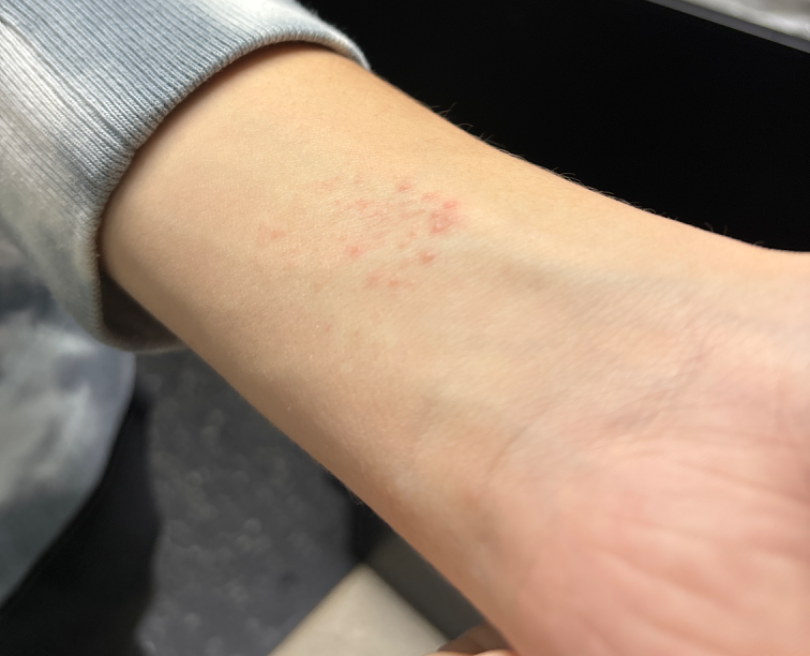History:
An image taken at an angle. The patient considered this acne. The affected area is the arm. Reported duration is about one day. The patient reports the lesion is fluid-filled and raised or bumpy. Skin tone: human graders estimated 3 on the Monk skin tone scale. No associated lesion symptoms were reported. Male subject, age 18–29.
Impression:
The reviewing clinician's impression was: Allergic Contact Dermatitis (leading).